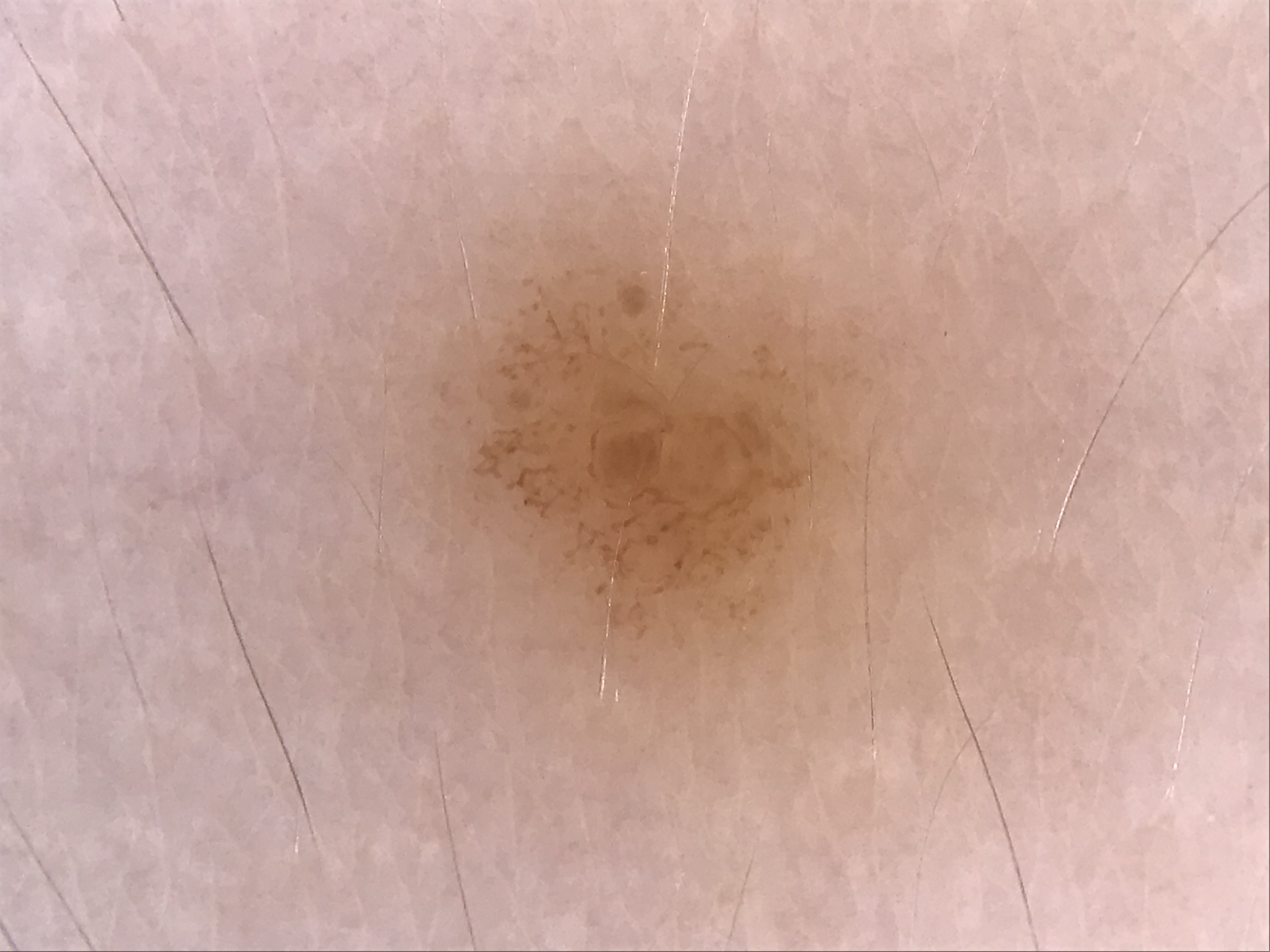A dermoscopic photograph of a skin lesion. The diagnosis was a benign lesion — a dysplastic junctional nevus.